A clinical photograph of a skin lesion · a subject in their 50s: 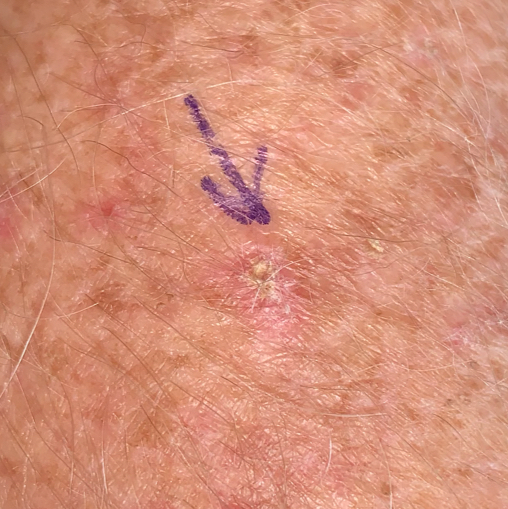The lesion involves a forearm.
By the patient's account, the lesion is elevated and itches.
Clinically diagnosed as an actinic keratosis.